A female subject, about 25 years old. A dermoscopic view of a skin lesion: 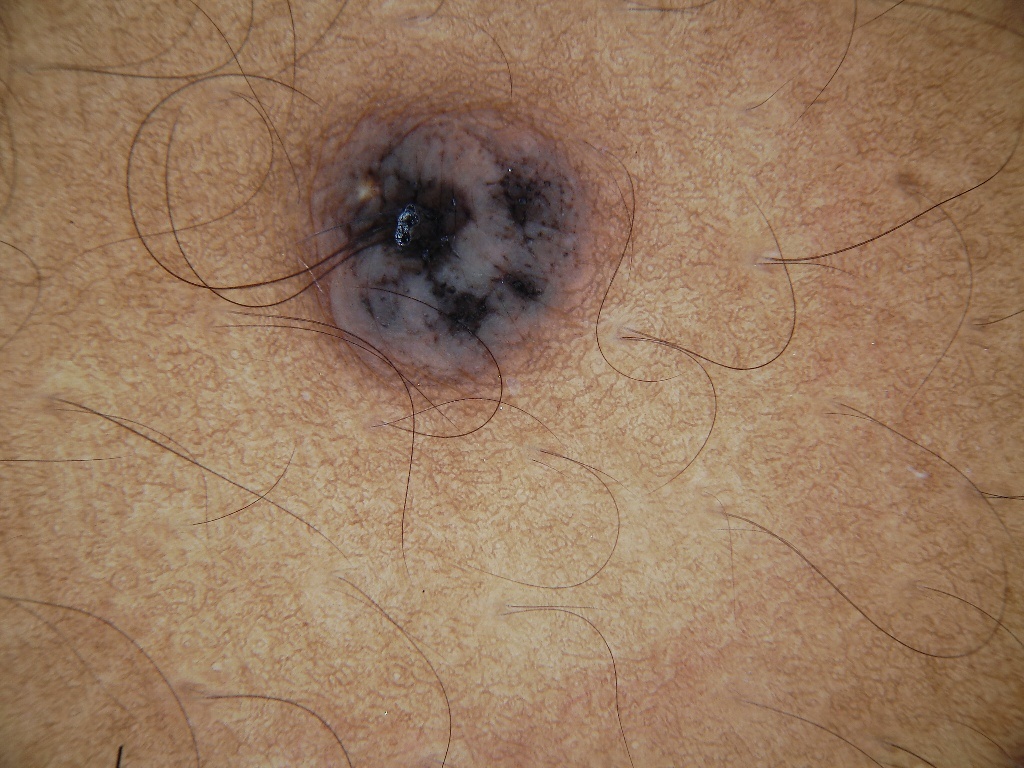dermoscopic features assessed but absent: streaks, milia-like cysts, negative network, globules, and pigment network; lesion size: ~9% of the field; lesion location: left=305, top=103, right=599, bottom=392; impression: a melanocytic nevus.